This is a close-up image: 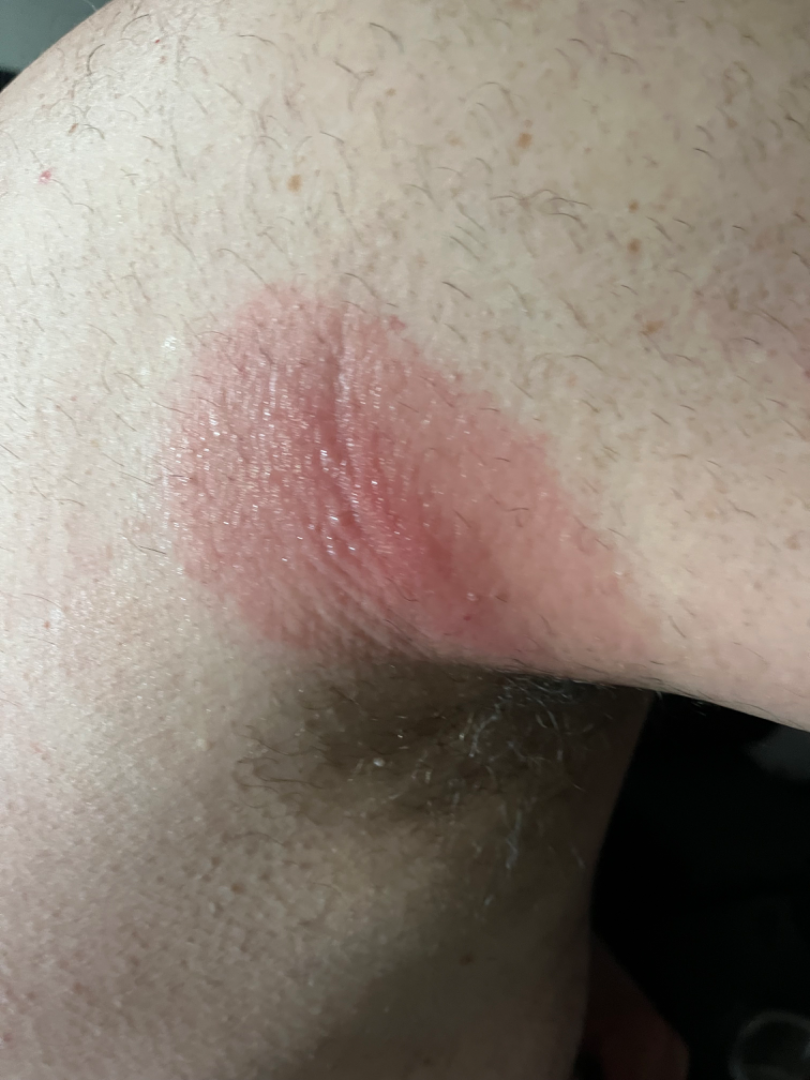The differential is split between Allergic Contact Dermatitis and Irritant Contact Dermatitis.